A dermoscopic image of a skin lesion.
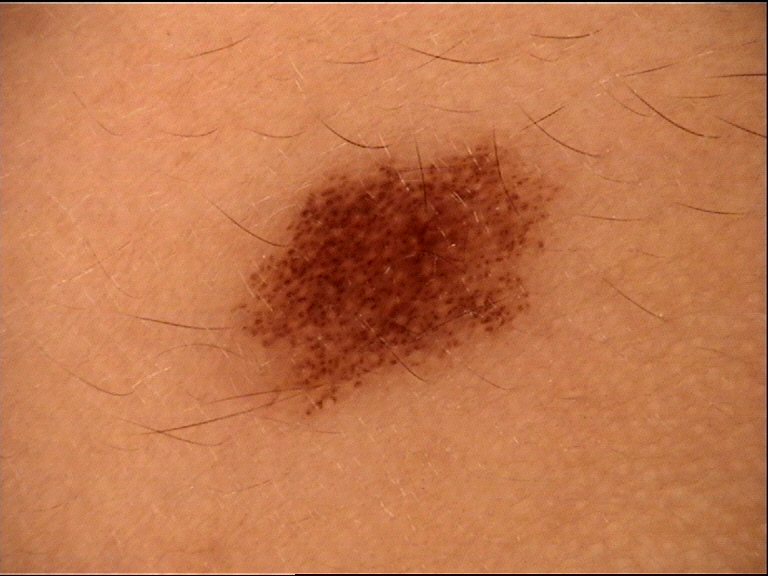Findings:
– diagnostic label: junctional nevus (expert consensus)